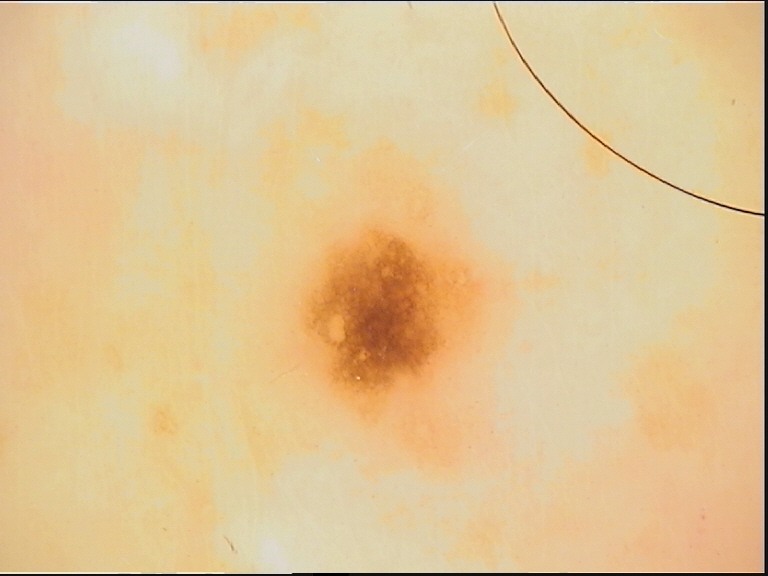Case:
* label — dysplastic junctional nevus (expert consensus)